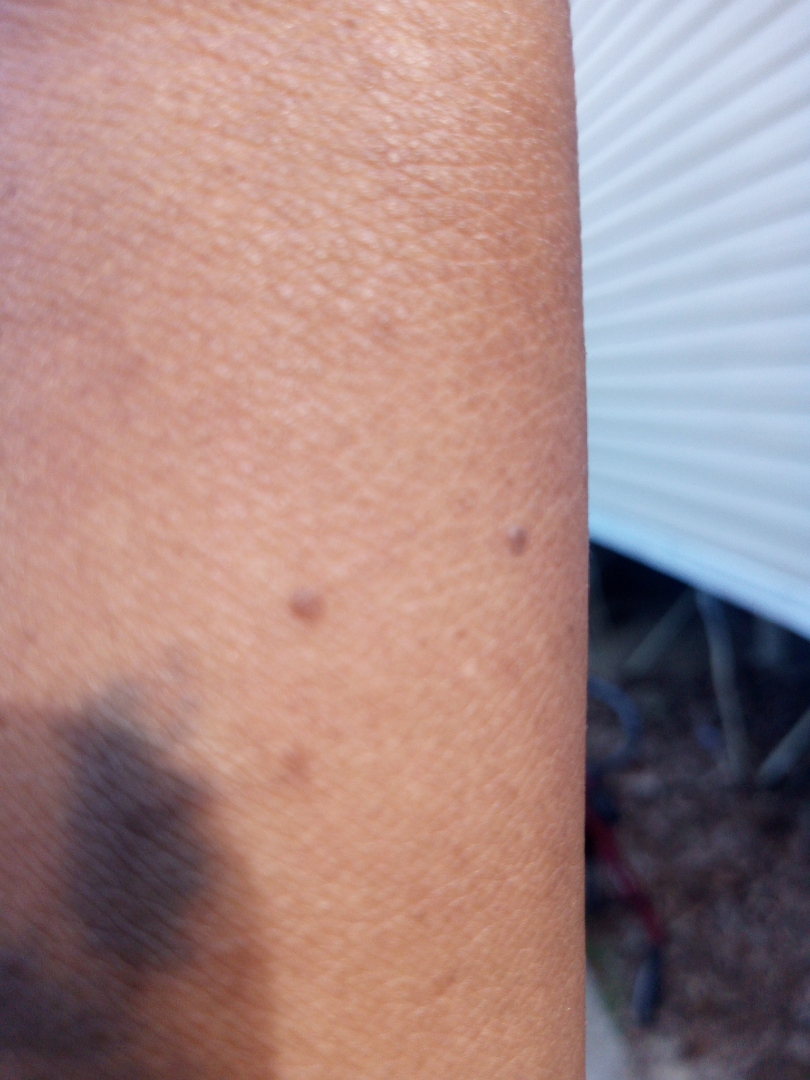Notes:
* assessment · not assessable
* symptom duration · one to three months
* anatomic site · arm and leg
* reported symptoms · bothersome appearance, pain, itching, burning, darkening and enlargement
* surface texture · raised or bumpy and flat
* patient's own categorization · a rash
* photo taken · at a distance